The lesion involves the front of the torso. This is a close-up image. The patient is 18–29, male:
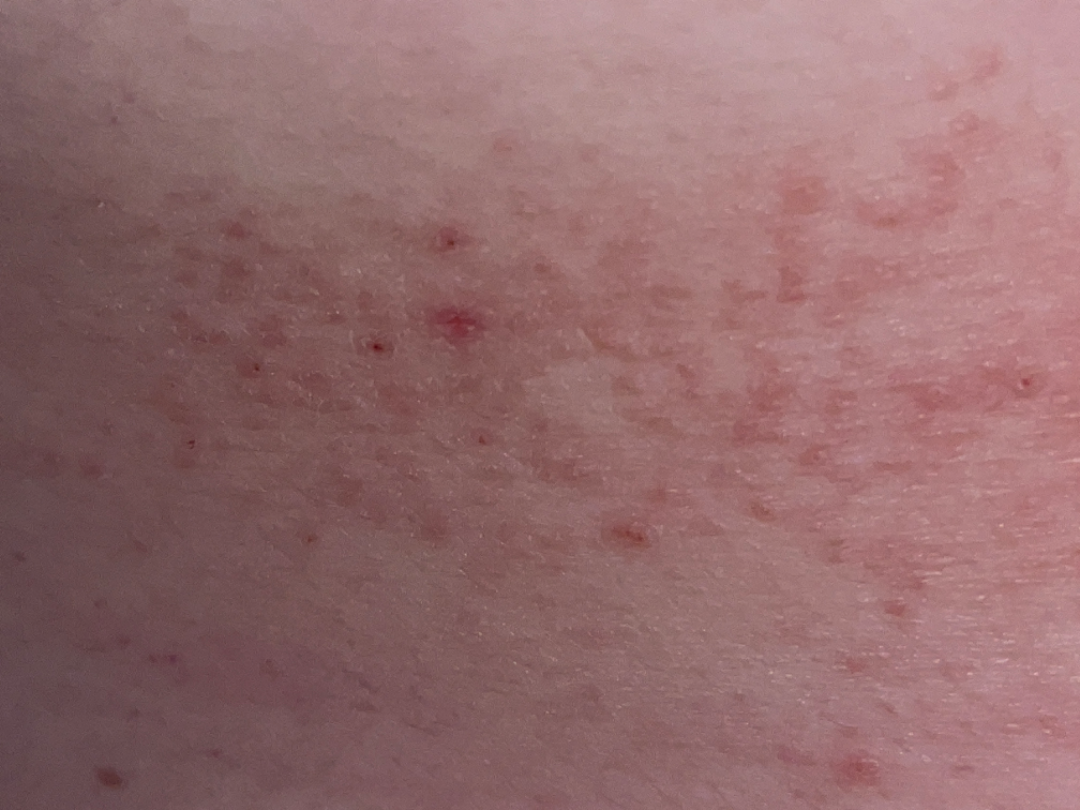A single dermatologist reviewed the case: the leading impression is Eczema; also raised was Folliculitis; possibly Allergic Contact Dermatitis.